A subject in their late 40s · a clinical close-up photograph of a skin lesion:
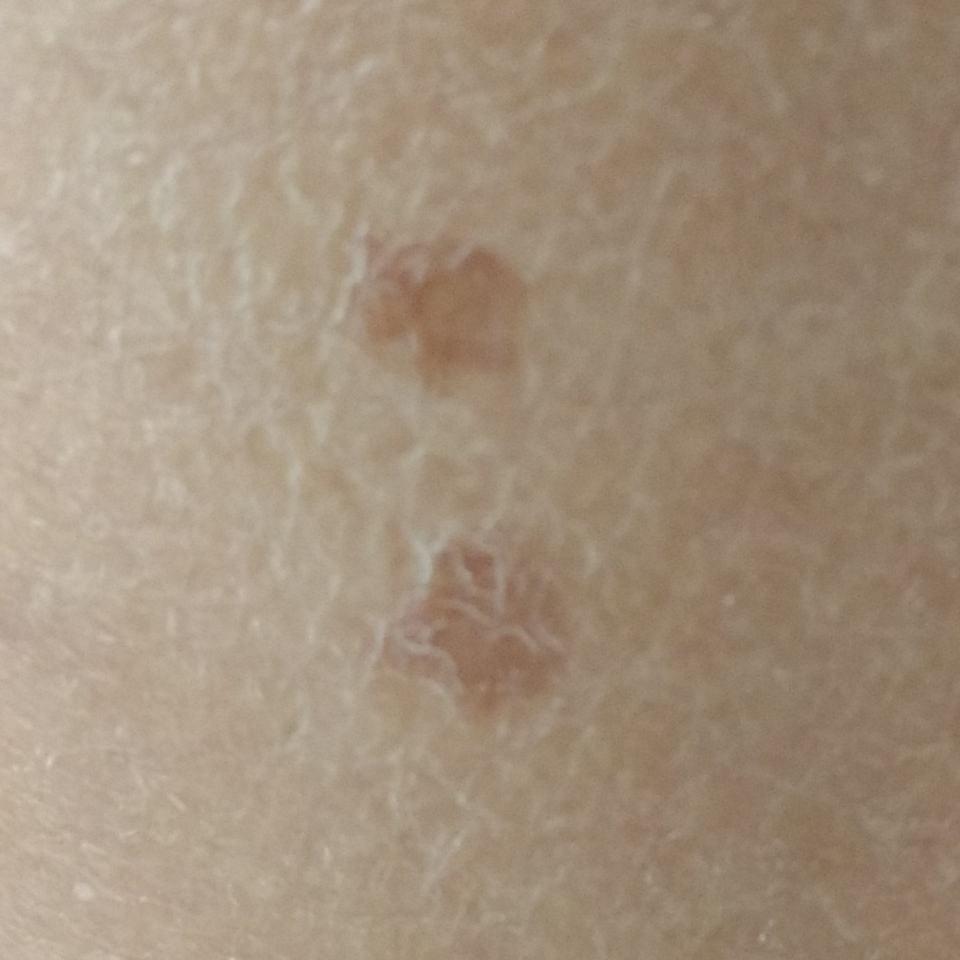lesion_location: a thigh
symptoms: none reported
diagnosis:
  name: seborrheic keratosis
  code: SEK
  malignancy: benign
  confirmation: clinical consensus